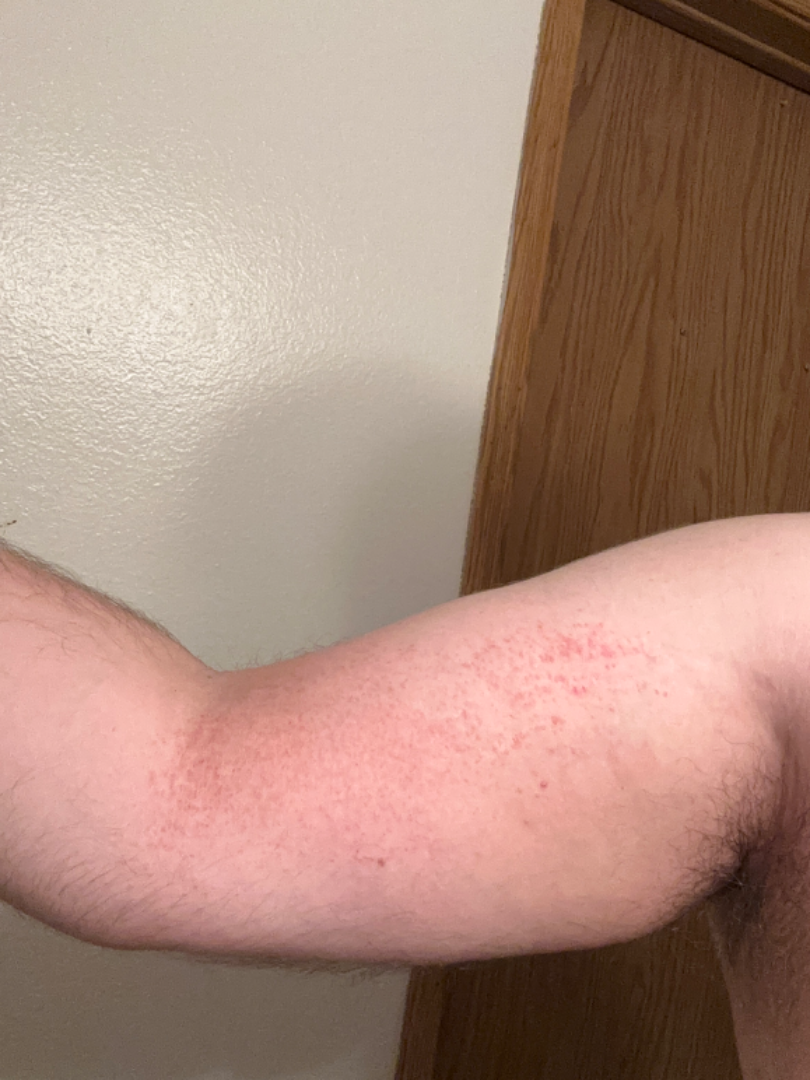Impression:
The skin condition could not be confidently assessed from this image.
History:
Male contributor, age 30–39. The condition has been present for one to four weeks. The patient considered this a rash. Located on the front of the torso and arm. The photograph was taken at a distance. Texture is reported as raised or bumpy. The lesion is associated with burning, itching, enlargement, pain and bothersome appearance.